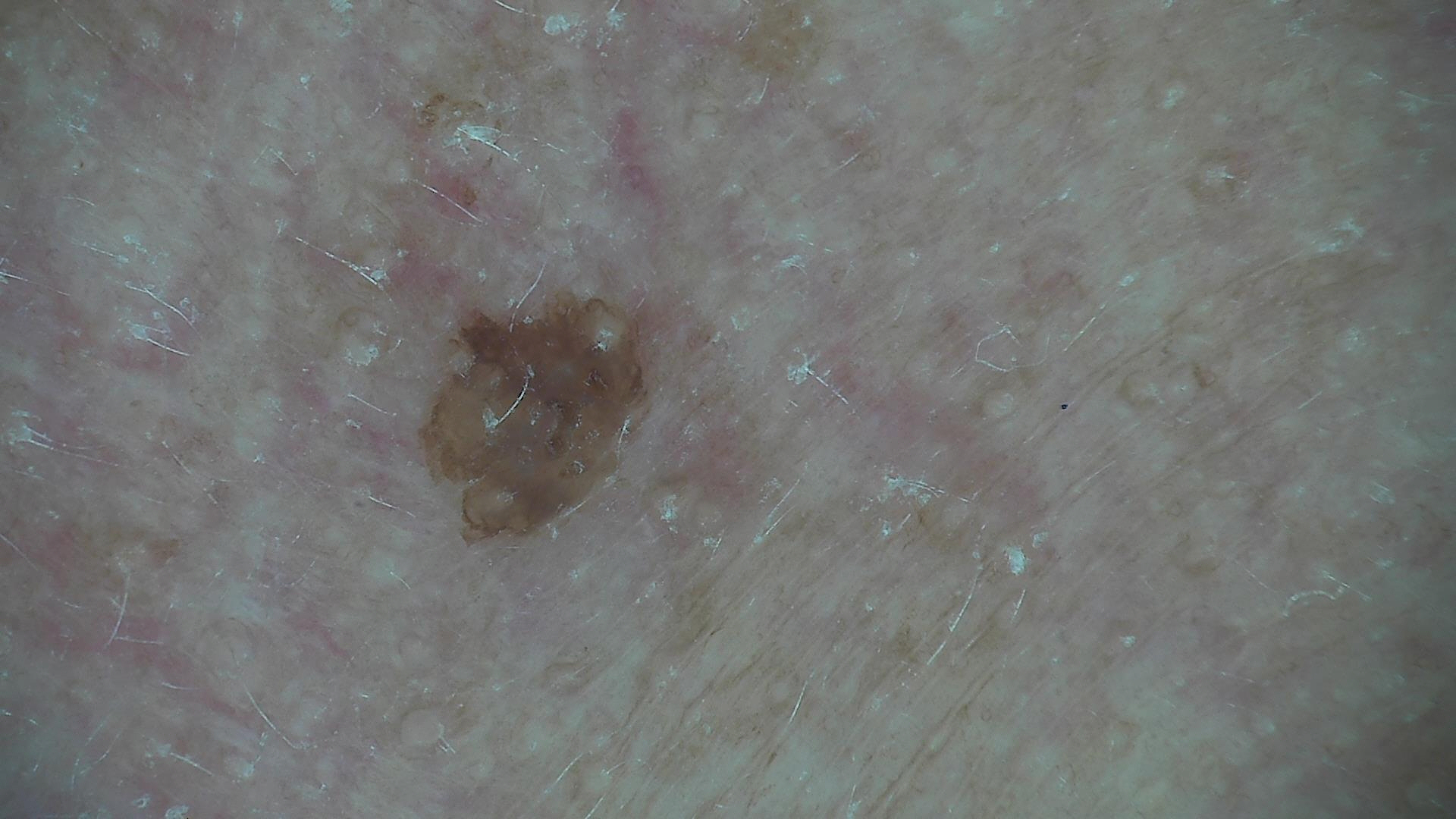Impression:
Labeled as a seborrheic keratosis.